A close-up photograph.
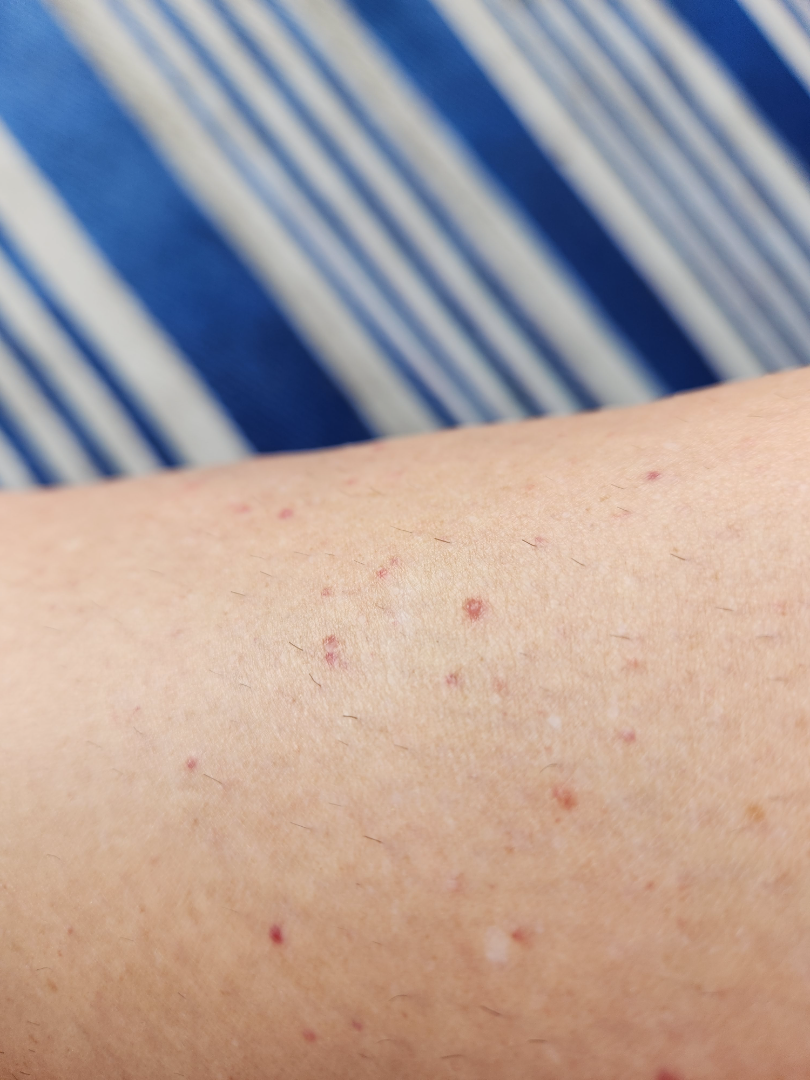* differential — one reviewing dermatologist: most consistent with petechiae